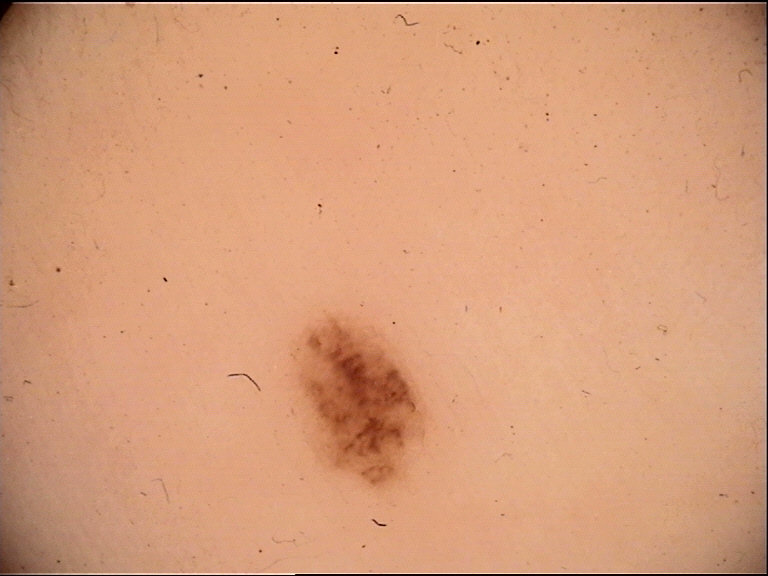Consistent with an acral compound nevus.